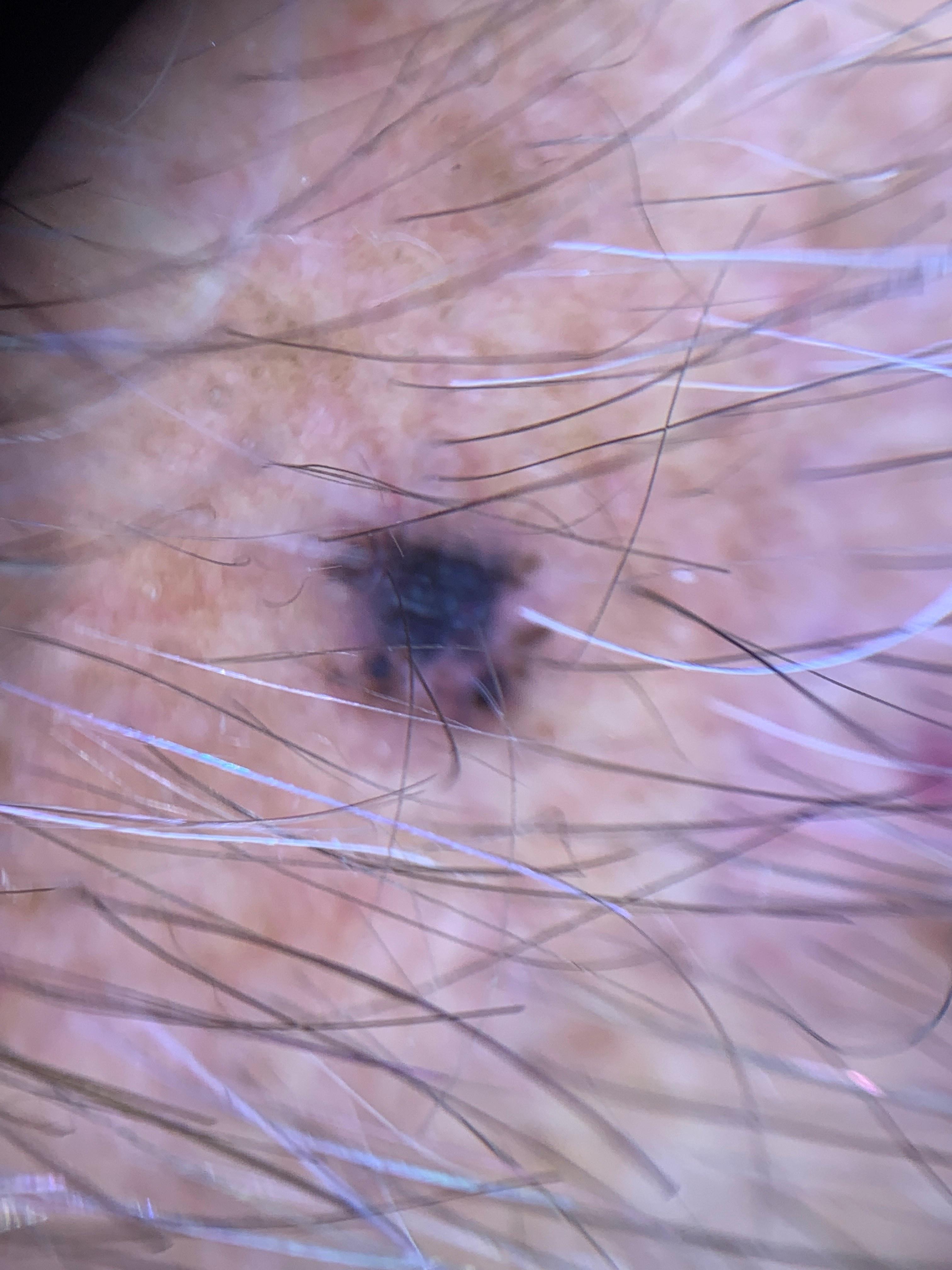<case>
  <skin_type>III</skin_type>
  <image>contact-polarized dermoscopy</image>
  <patient>
    <age_approx>85+</age_approx>
    <sex>male</sex>
  </patient>
  <lesion_location>
    <region>the head or neck</region>
  </lesion_location>
  <diagnosis>
    <name>Basal cell carcinoma</name>
    <malignancy>malignant</malignancy>
    <confirmation>histopathology</confirmation>
    <lineage>adnexal</lineage>
  </diagnosis>
</case>